A skin lesion imaged with a dermatoscope.
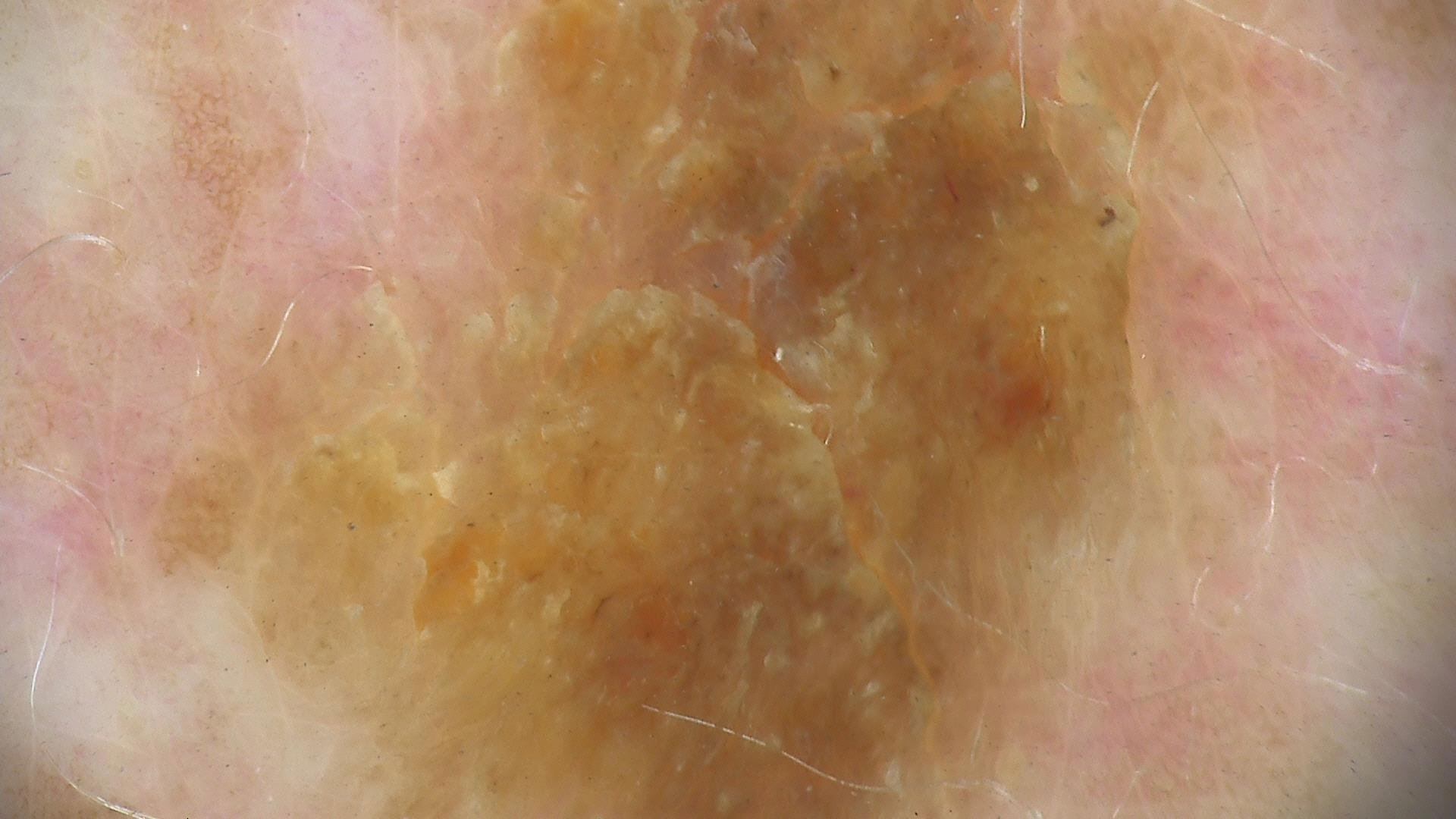Case:
The morphology is that of a keratinocytic lesion.
Impression:
Diagnosed as a seborrheic keratosis.